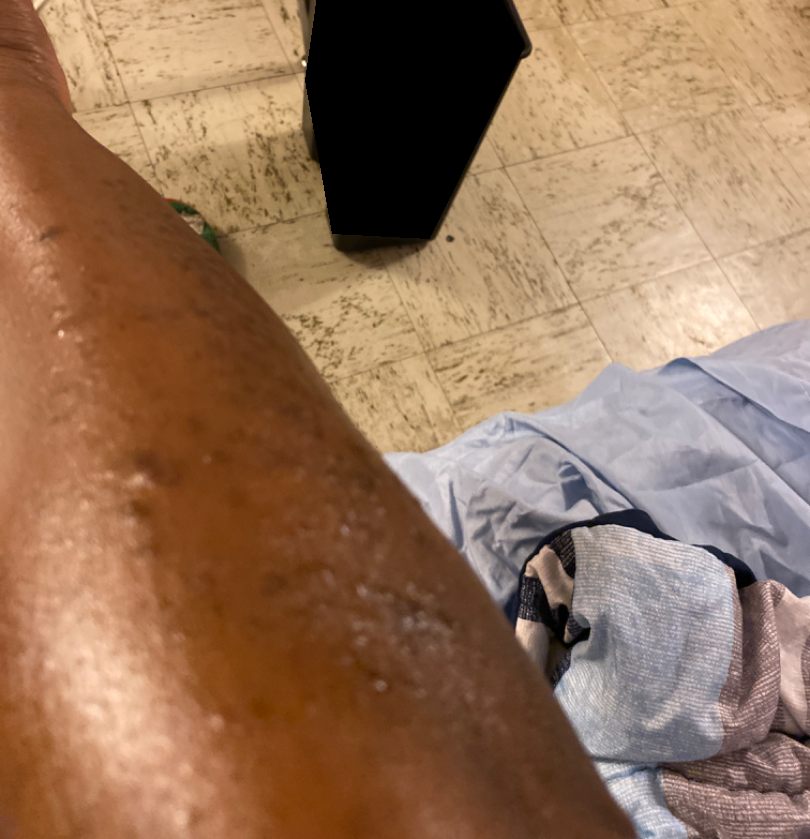assessment: indeterminate from the photograph | view: close-up | lesion texture: raised or bumpy and rough or flaky.